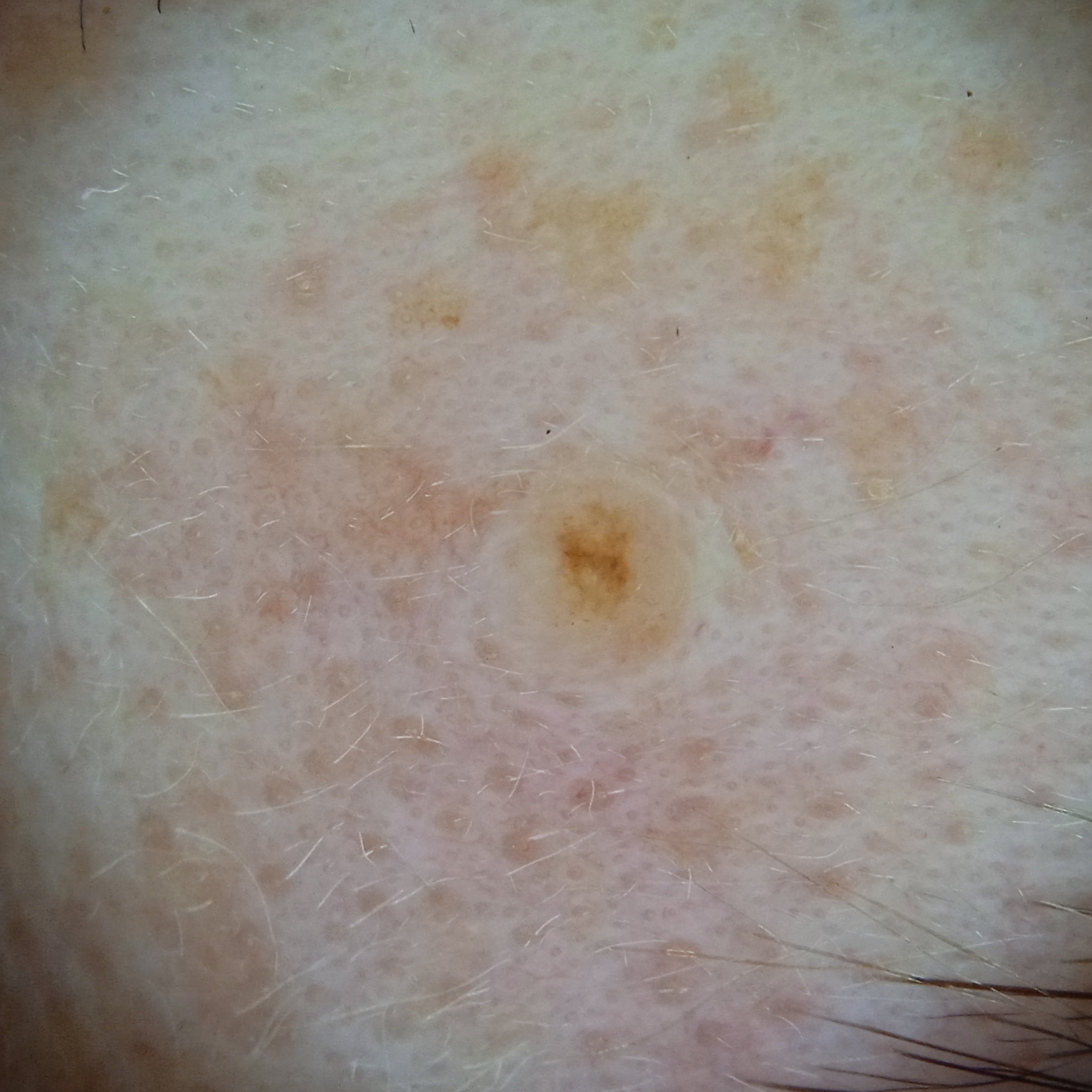referral: clinical suspicion of melanoma, nevus count: a moderate number of melanocytic nevi, image type: dermatoscopic image, site: the face, assessment: melanocytic nevus (dermatologist consensus).